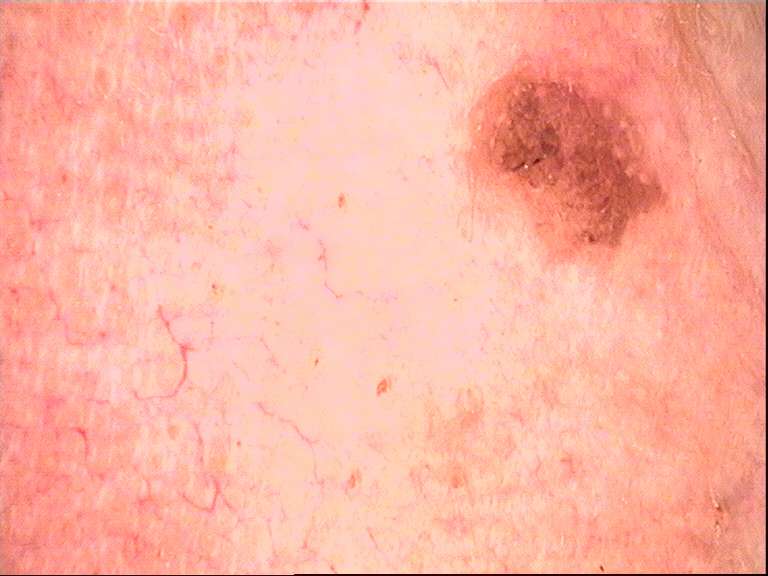{"diagnosis": {"name": "seborrheic keratosis", "code": "sk", "malignancy": "benign", "super_class": "non-melanocytic", "confirmation": "expert consensus"}}